Located on the head or neck · self-categorized by the patient as skin that appeared healthy to them · close-up view · no relevant systemic symptoms · Fitzpatrick skin type IV; non-clinician graders estimated 2 on the MST: 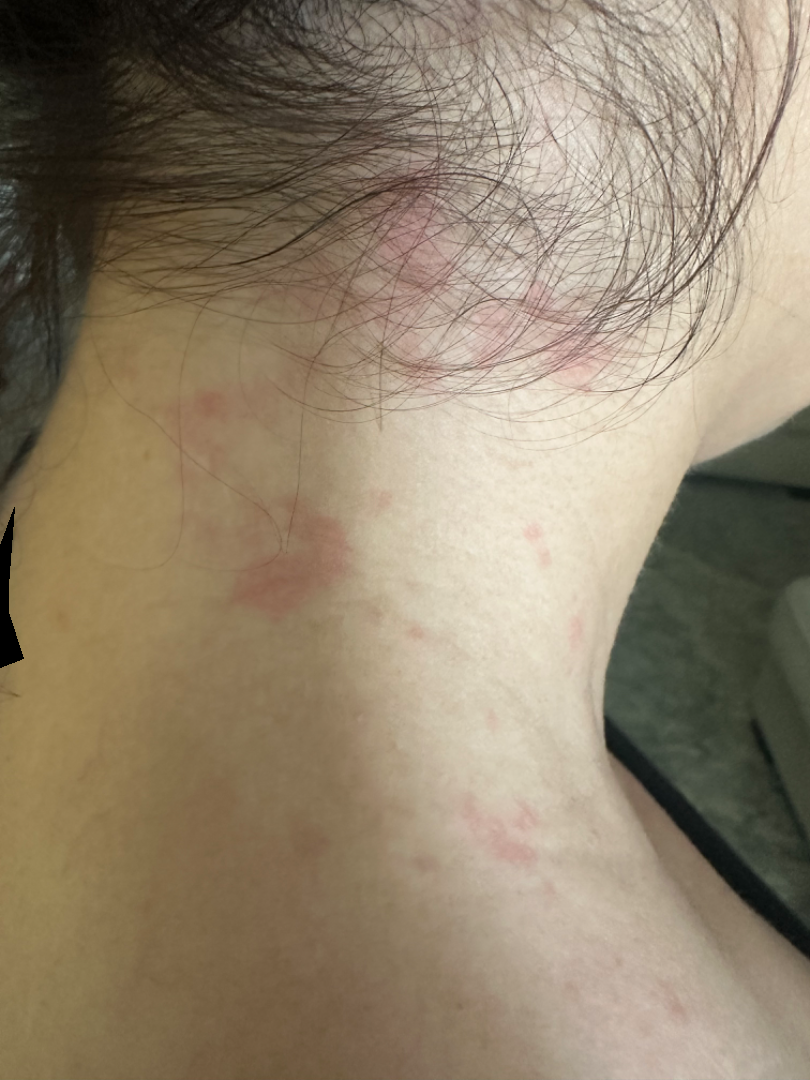The dermatologist could not determine a likely condition from the photograph alone.